The leg is involved · this is a close-up image: 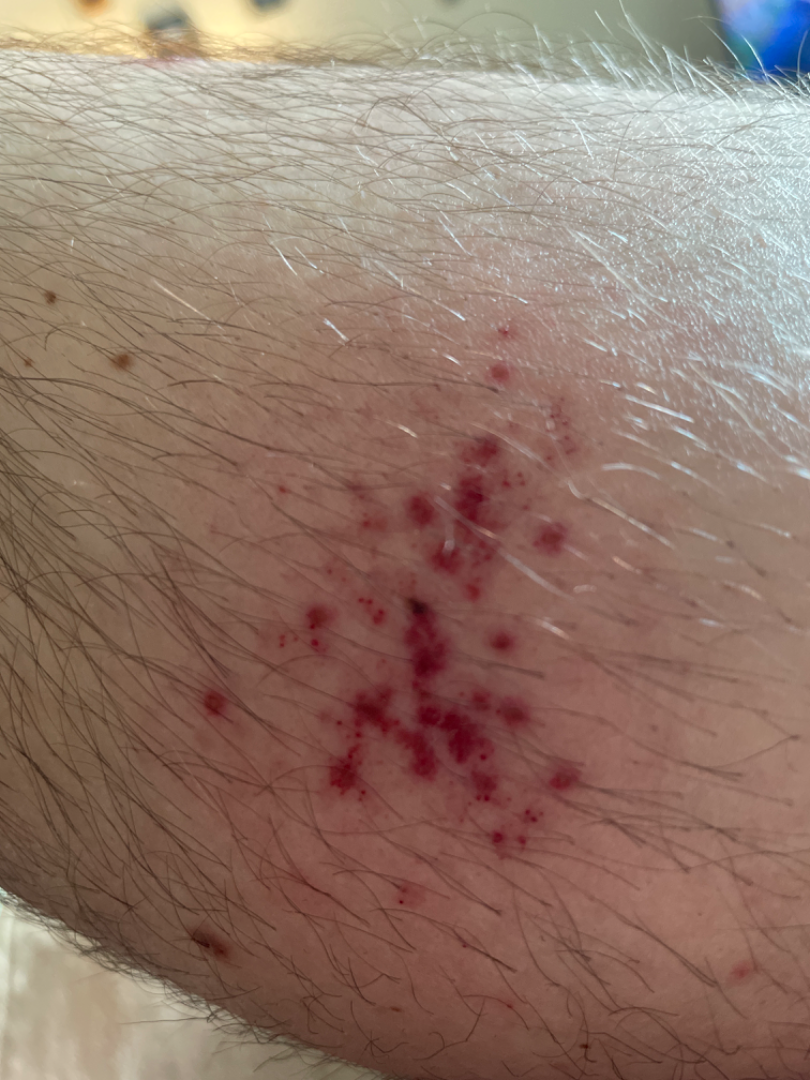On remote review of the image: favoring Leukocytoclastic Vasculitis; also raised was Herpes Zoster.